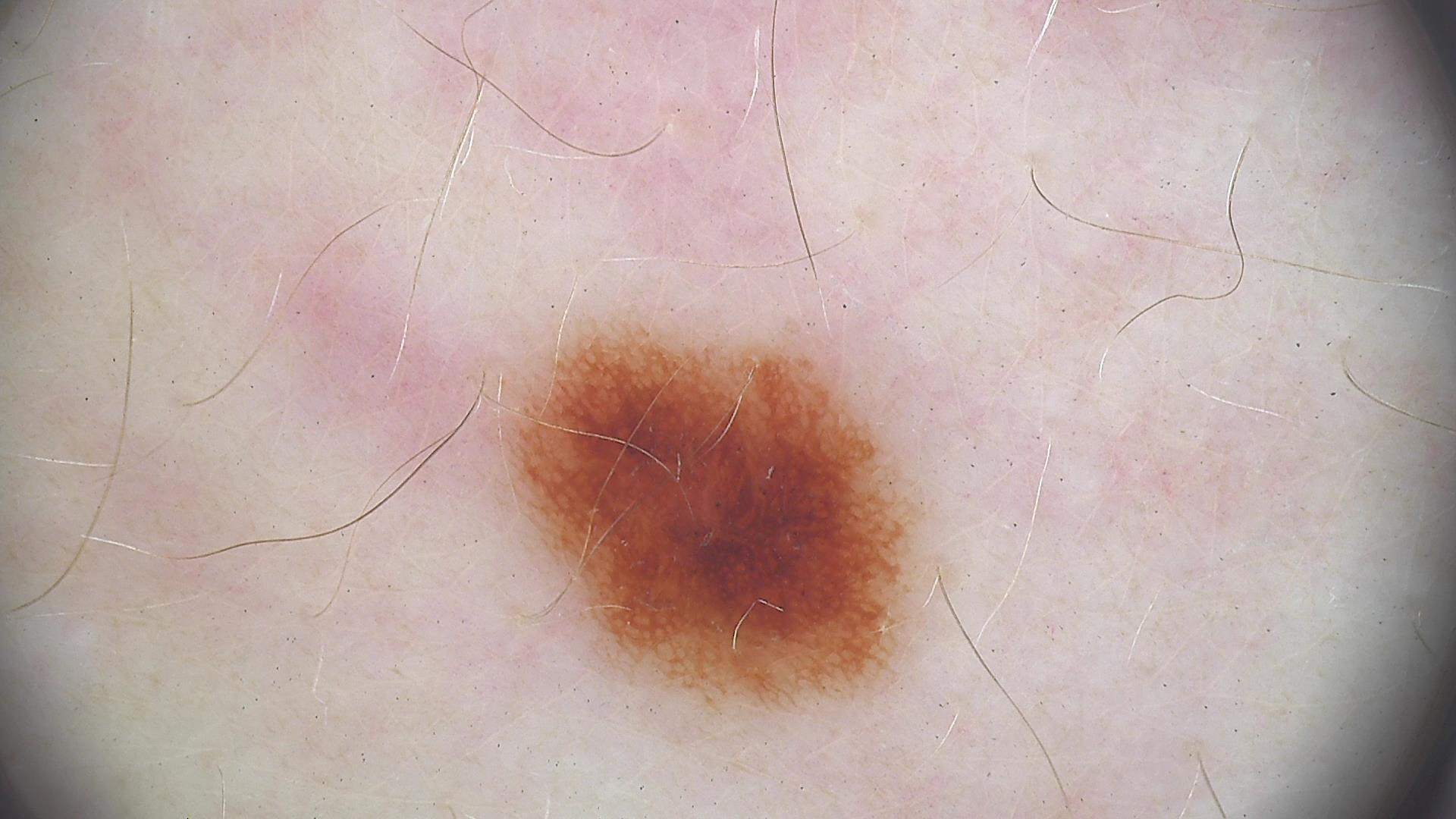Consistent with a dysplastic junctional nevus.